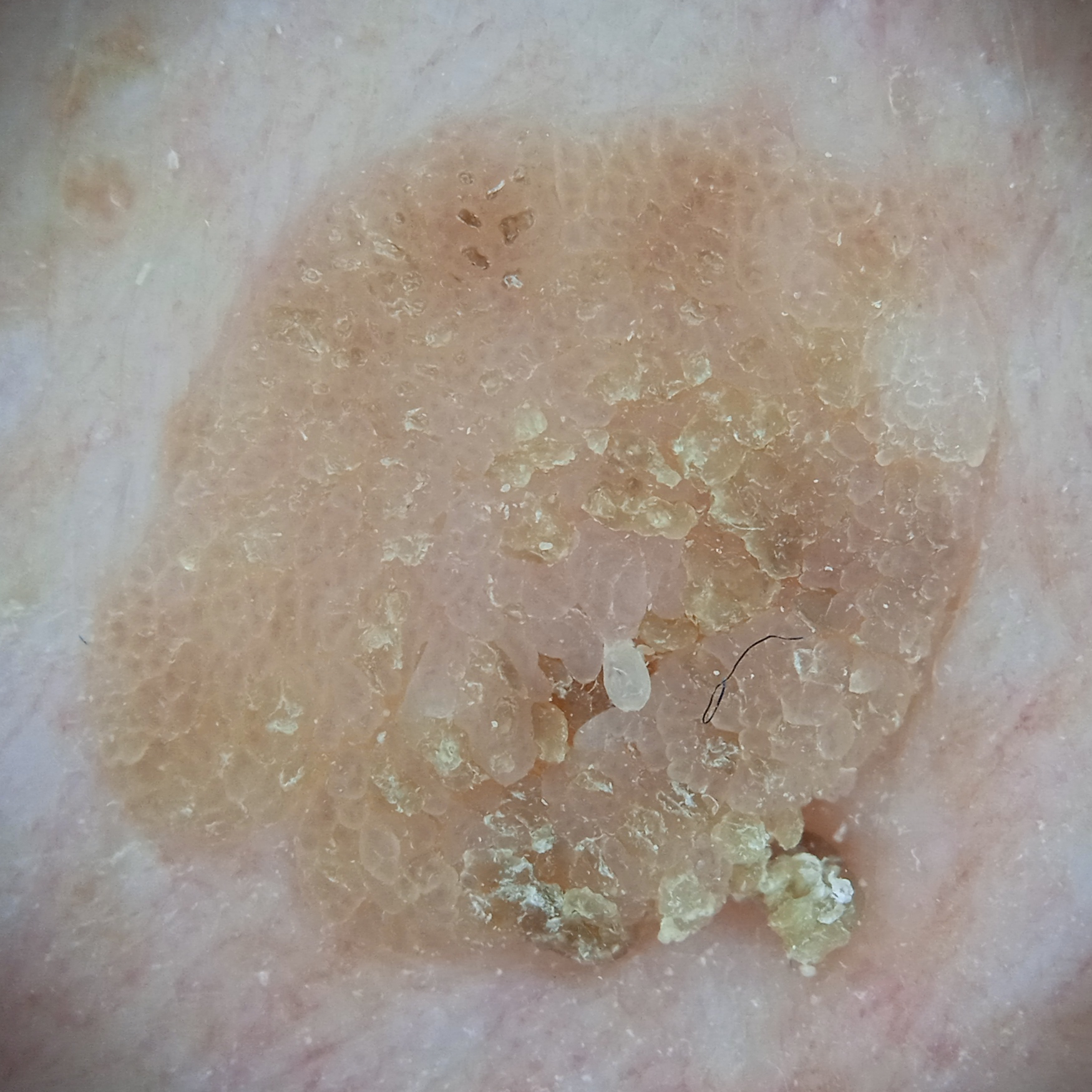Conclusion:
The lesion was assessed as a seborrheic keratosis.